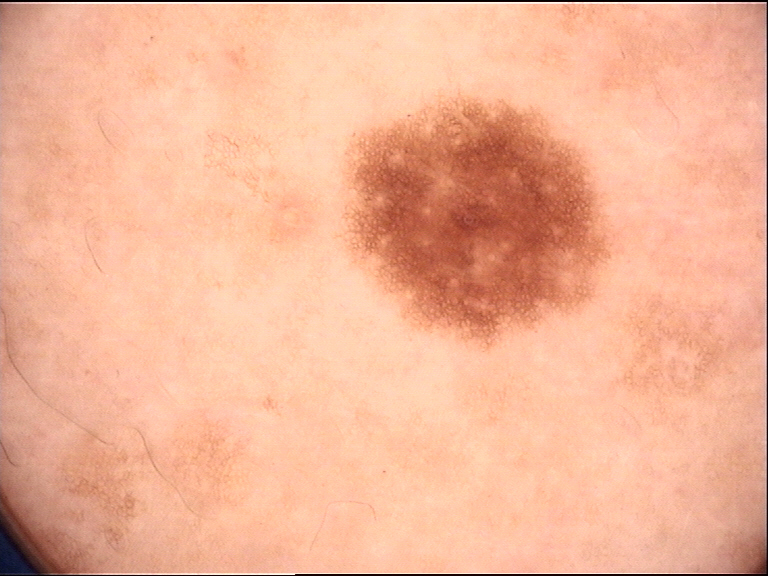Findings:
A dermatoscopic image of a skin lesion.
Impression:
Labeled as a dysplastic junctional nevus.